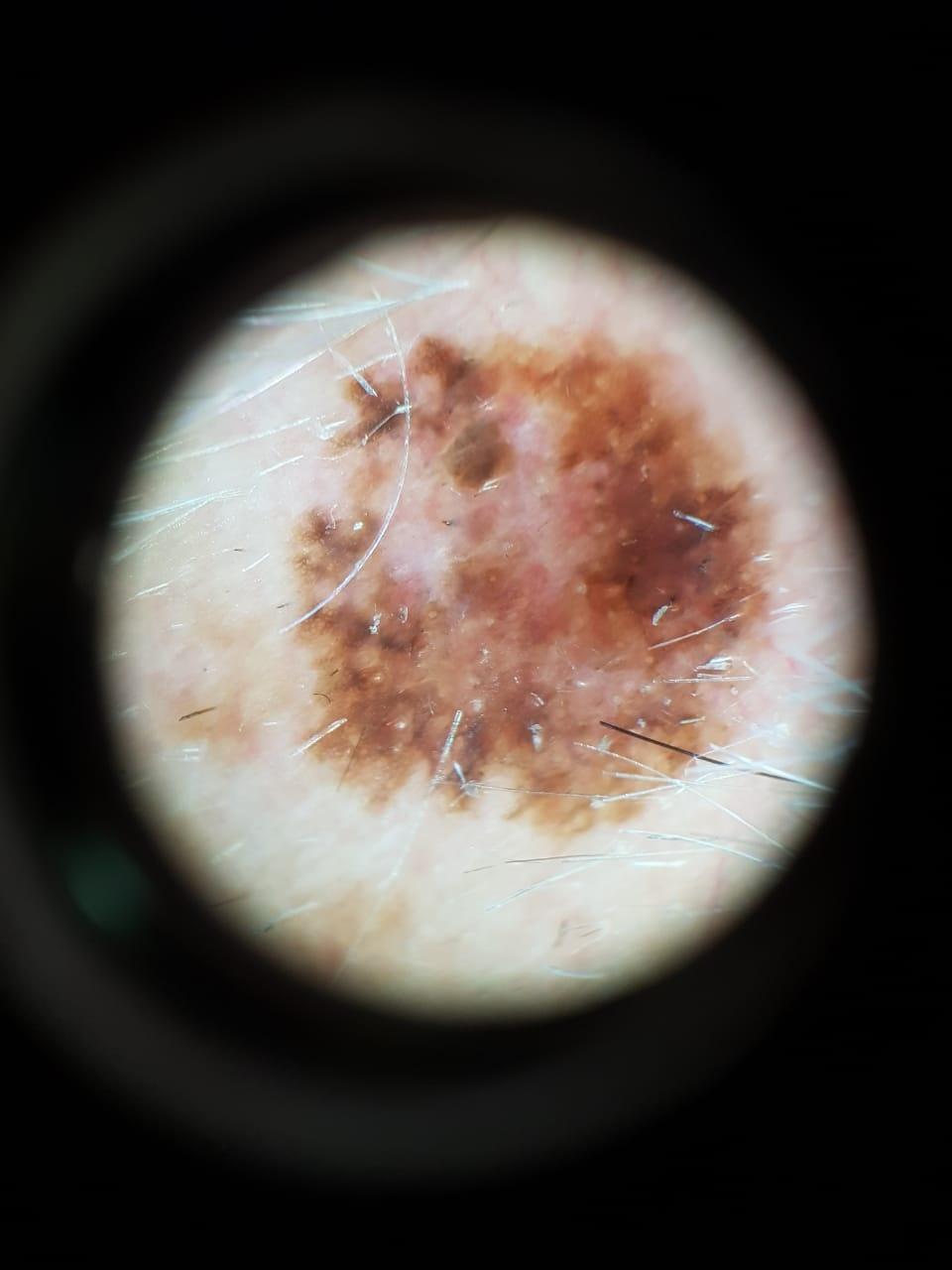Contact-polarized dermoscopy of a skin lesion. A male patient aged 73 to 77. The lesion involves the head or neck. Histopathologically confirmed as a melanoma.